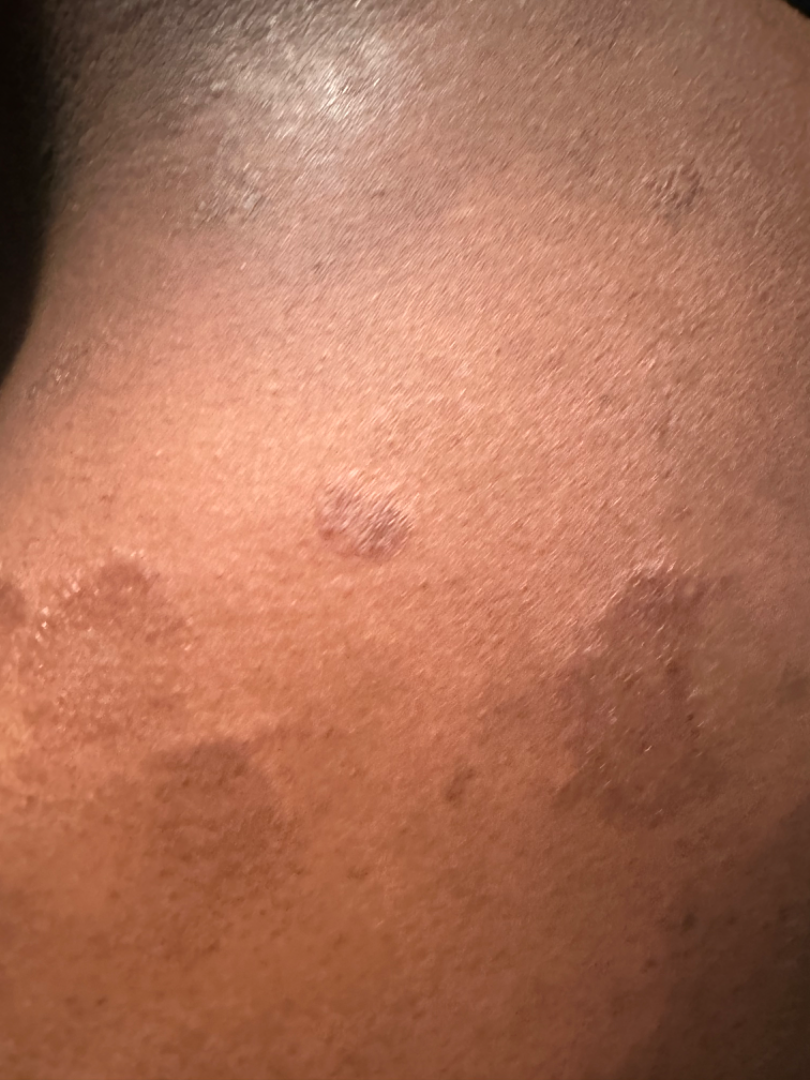assessment: could not be assessed | shot type: close-up.